Dermoscopy of a skin lesion.
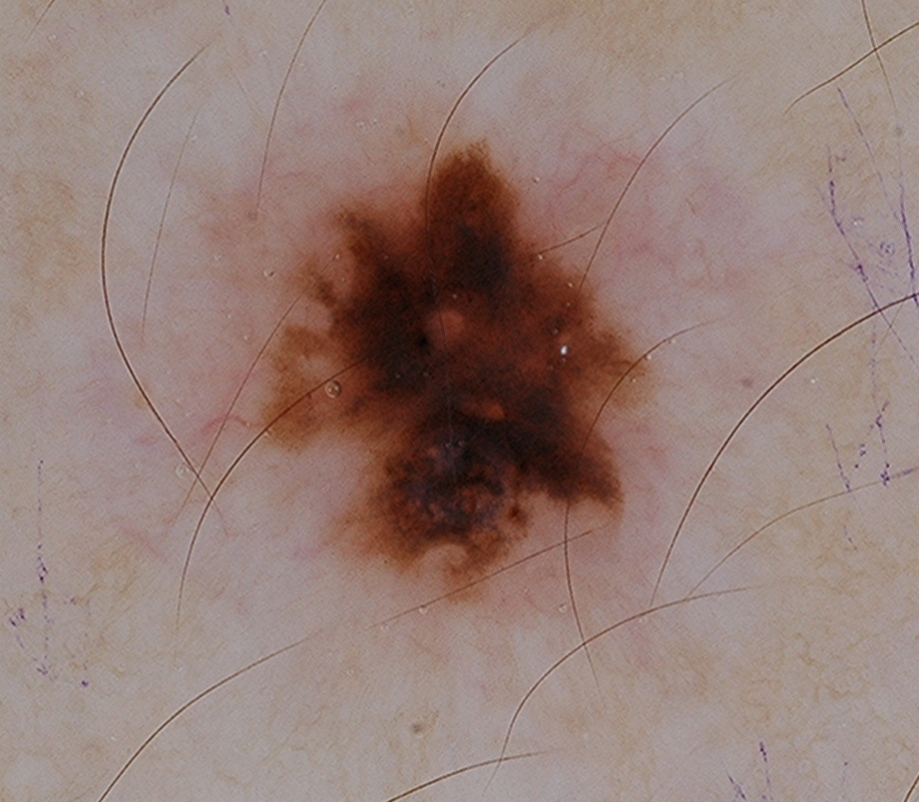Dermoscopic review identifies no streaks, globules, negative network, pigment network, or milia-like cysts.
The lesion covers approximately 17% of the dermoscopic field.
As (left, top, right, bottom), the lesion's extent is 249 128 664 604.
Biopsy-confirmed as a melanoma.